The patient is a female aged 30–39. The photograph is a close-up of the affected area:
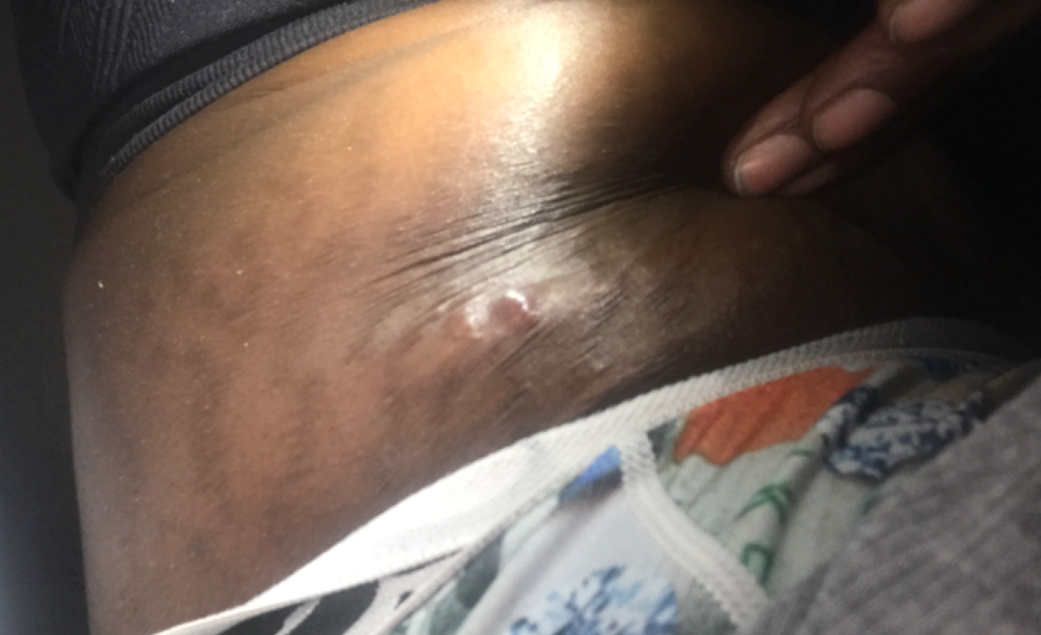The patient indicates the lesion is fluid-filled. Single-reviewer assessment: the differential, in no particular order, includes Abscess and Cyst.